The photograph was taken at a distance:
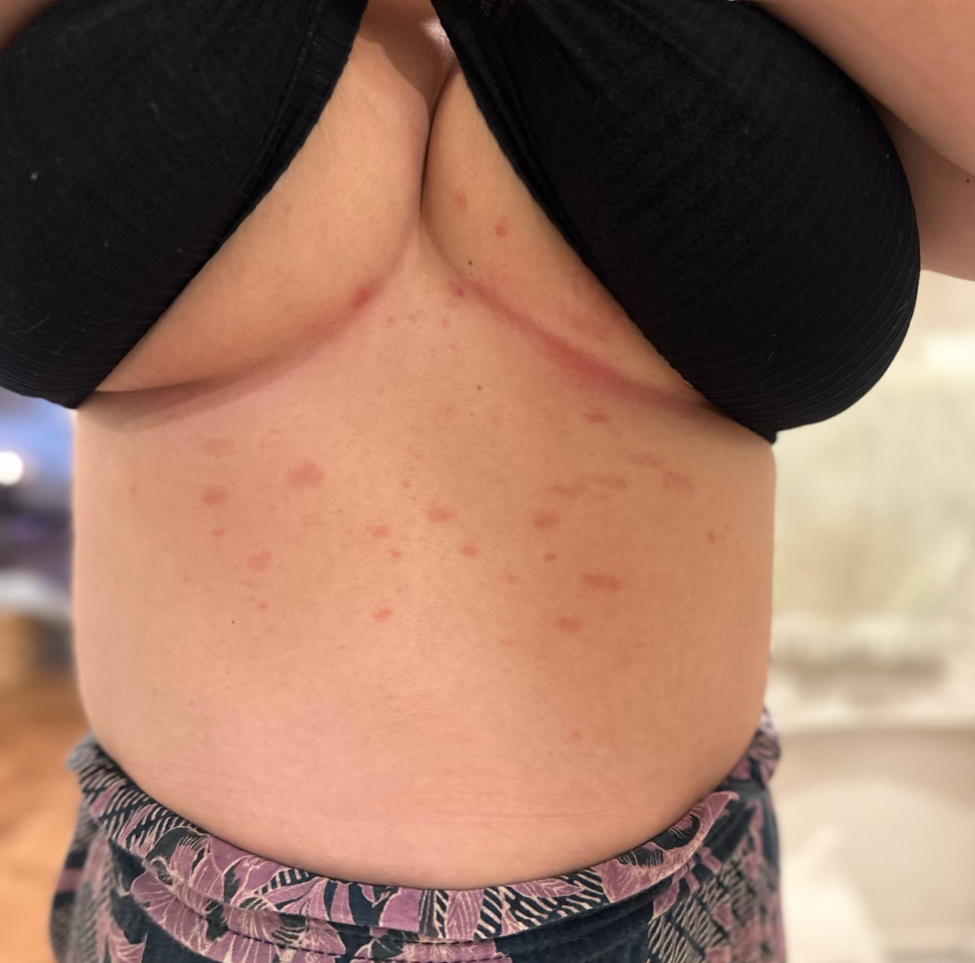{
  "systemic_symptoms": "none reported",
  "skin_tone": {
    "fitzpatrick": "I",
    "monk_skin_tone": 3
  },
  "texture": "flat",
  "symptoms": "none reported",
  "duration": "less than one week",
  "differential": "Pityriasis rosea"
}